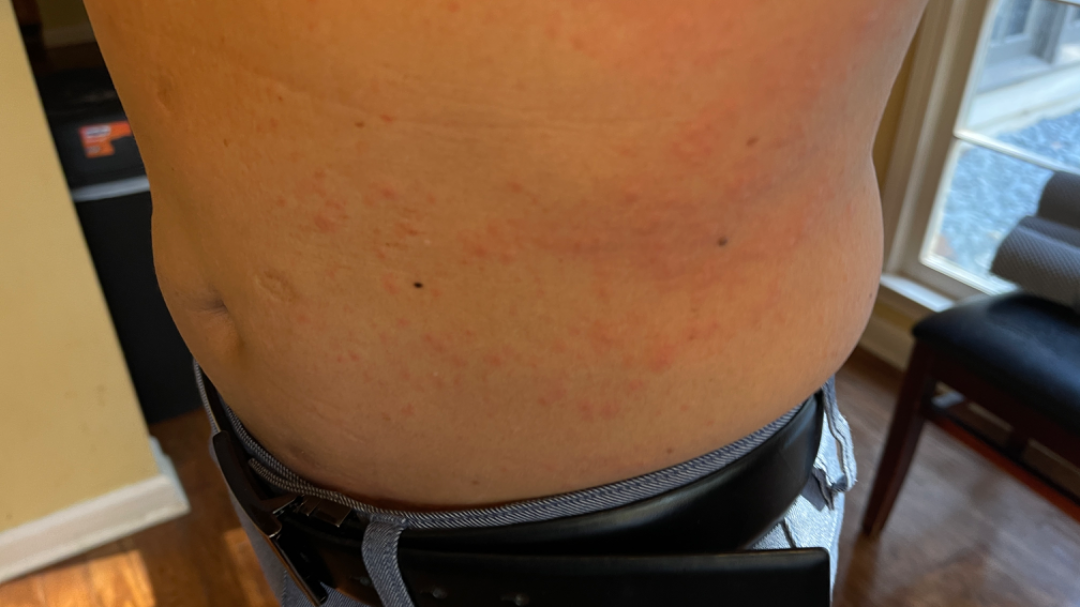<dermatology_case>
  <differential>Urticaria</differential>
</dermatology_case>